The patient describes having few moles overall · a female patient aged 60 · the patient reports a personal history of cancer and a personal history of skin cancer · the referring clinician suspected basal cell carcinoma · dermoscopy of a skin lesion · the patient says their skin tans without first burning: 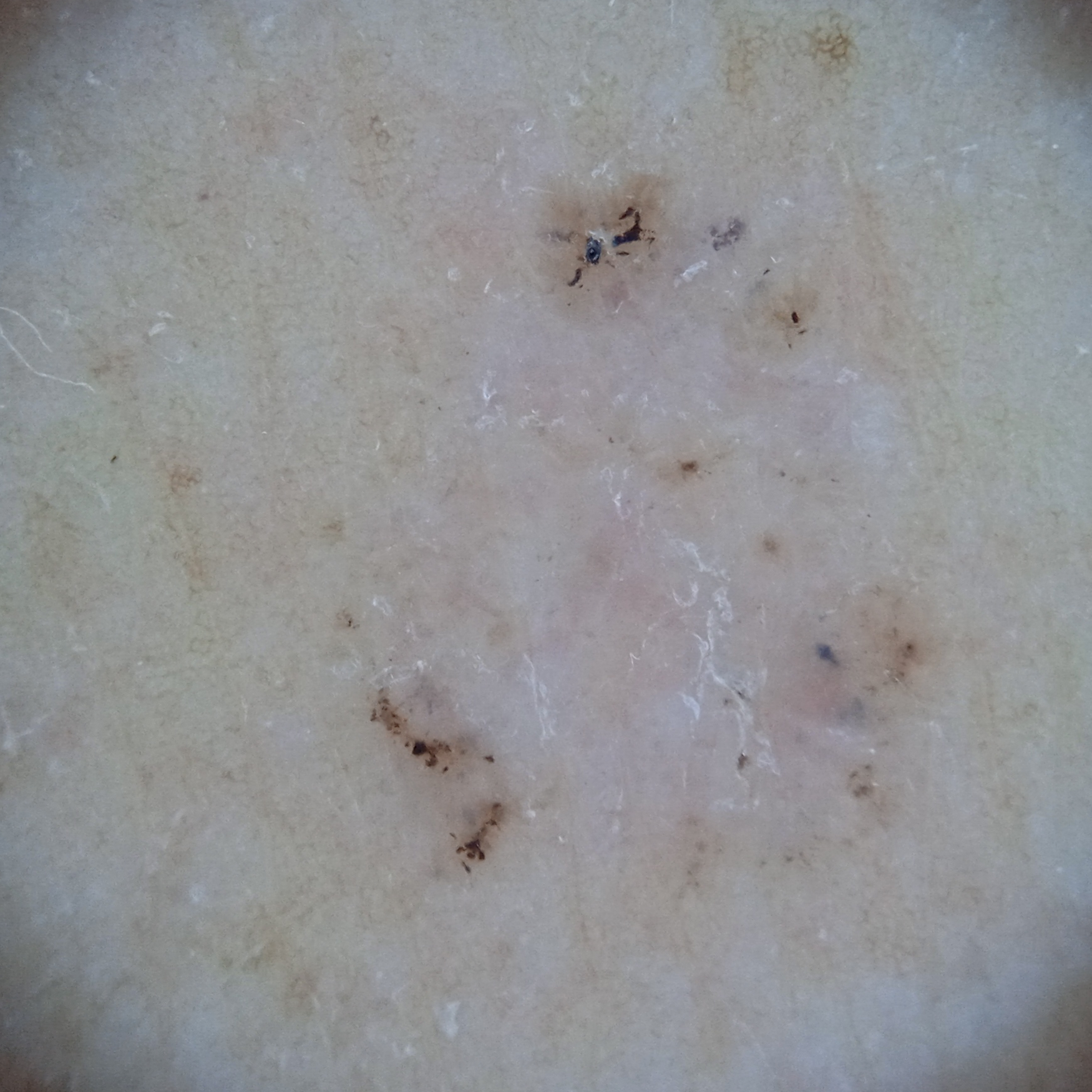<case>
  <lesion_location>the back</lesion_location>
  <lesion_size>
    <diameter_mm>7.8</diameter_mm>
  </lesion_size>
  <diagnosis>
    <name>basal cell carcinoma</name>
    <malignancy>malignant</malignancy>
  </diagnosis>
</case>